A clinical photograph of a skin lesion. A patient aged 75:
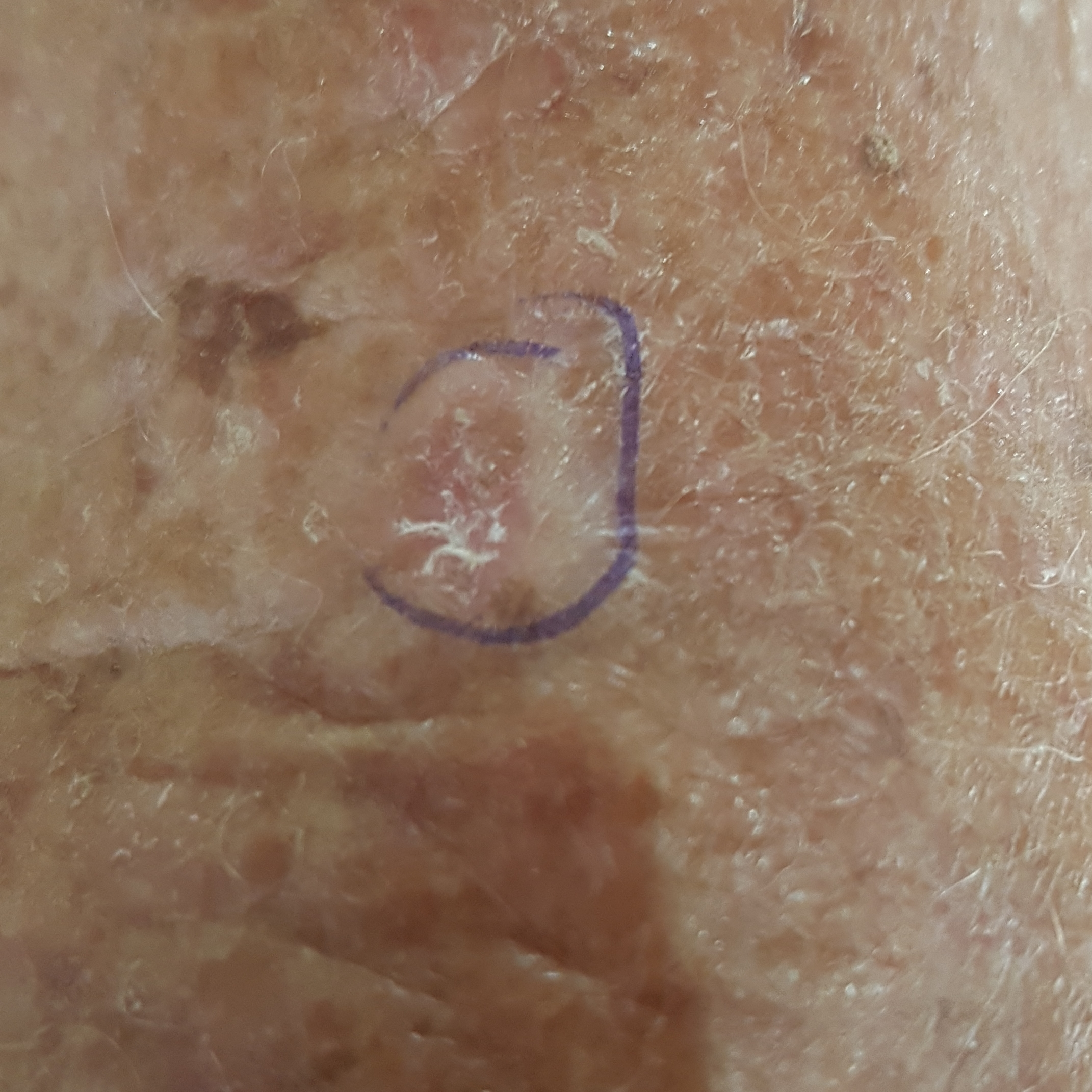The lesion is on a forearm.
By the patient's account, the lesion has grown, is elevated, and itches.
The clinical impression was an actinic keratosis.